The lesion involves the top or side of the foot and leg; the photo was captured at a distance — 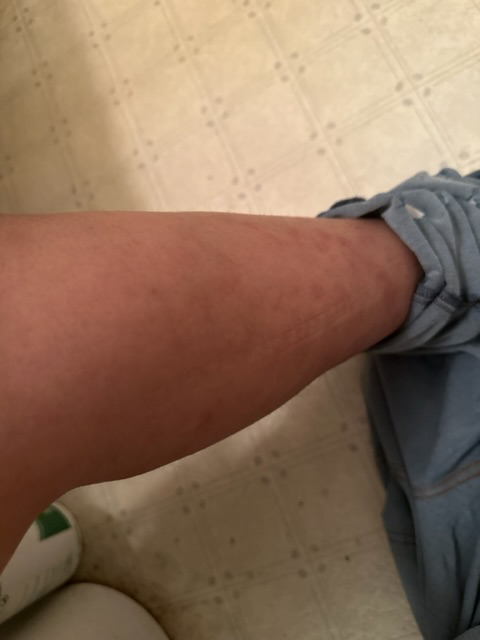Review:
The condition could not be reliably identified from the image.
Patient information:
The patient considered this a rash. The condition has been present for one to three months. Reported lesion symptoms include bothersome appearance, enlargement and darkening. The patient also reports fever.